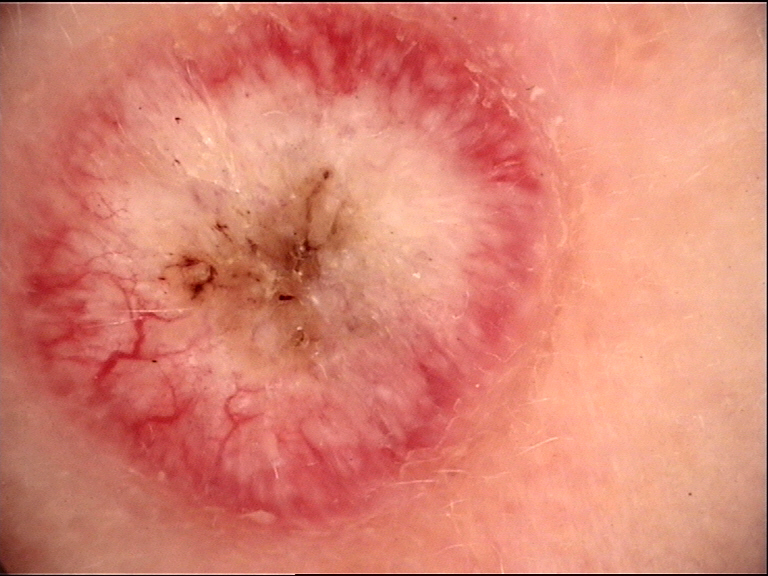modality = dermatoscopy; category = keratinocytic; diagnostic label = squamous cell carcinoma (biopsy-proven).